The photograph was taken at an angle · the contributor is 18–29, female · the arm is involved: 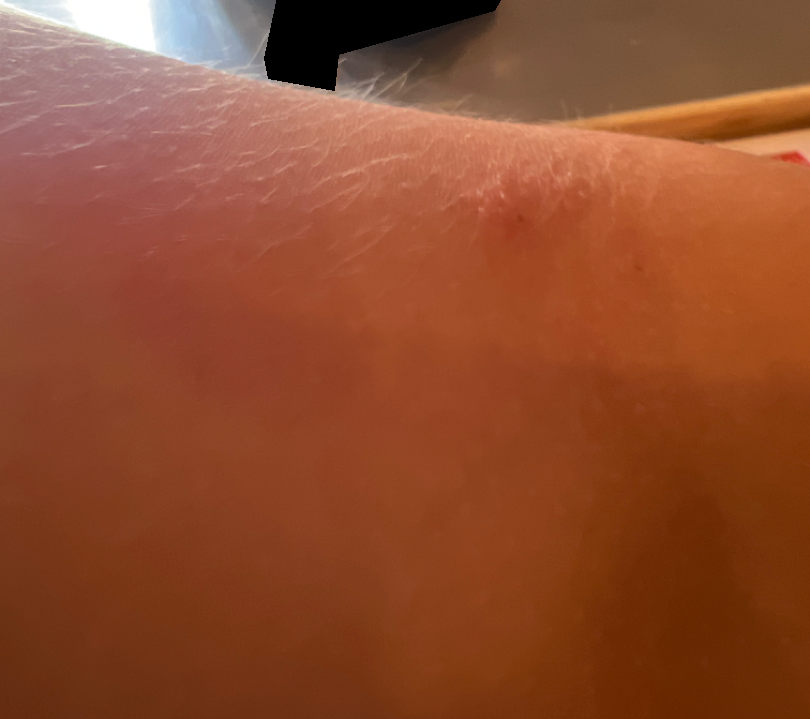| key | value |
|---|---|
| assessment | could not be assessed |